On a questionnaire the patient reported a personal history of skin cancer · dermoscopy of a skin lesion · the patient says their skin reddens with sun exposure · imaged for a research study, with no referral diagnosis recorded:
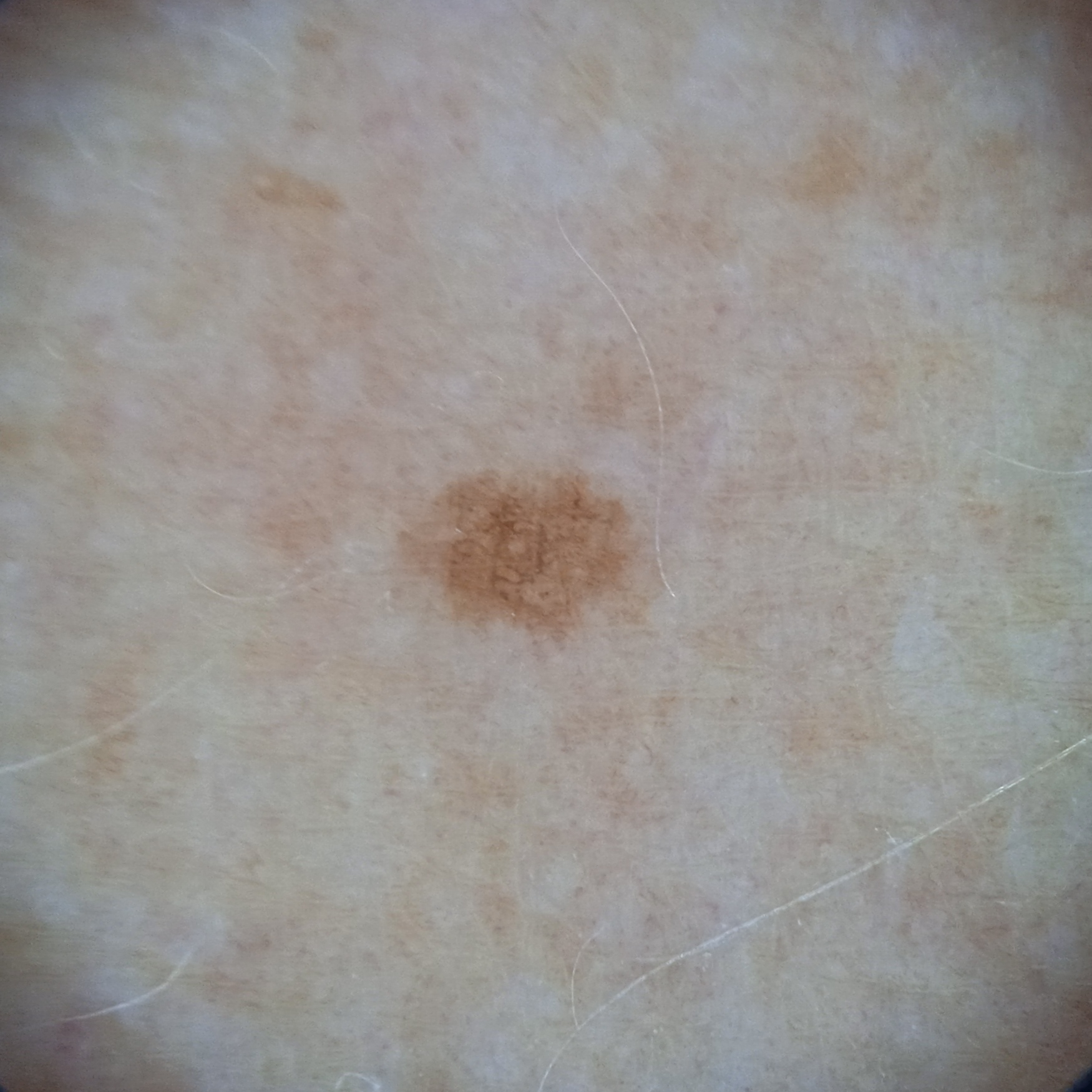Measuring roughly 2.3 mm.
The diagnostic impression was a melanocytic nevus.